Close-up view: 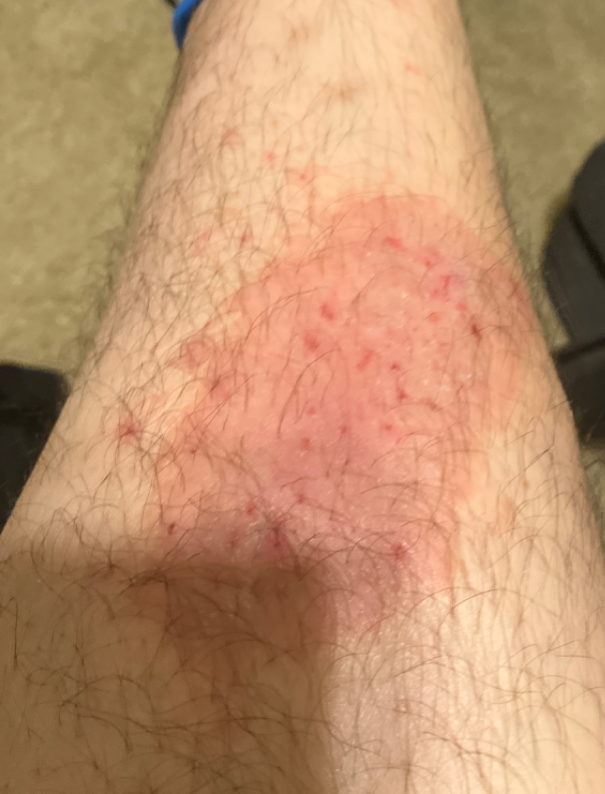The skin findings could not be characterized from the image.